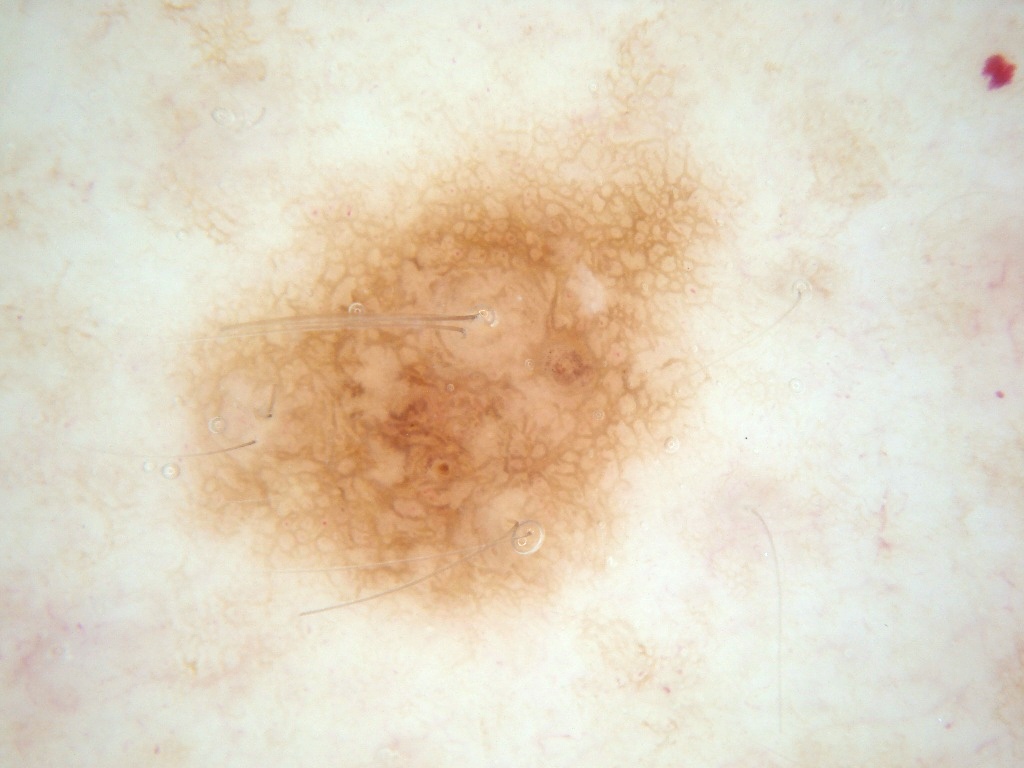<lesion>
<image>
  <modality>dermoscopy</modality>
</image>
<patient>
  <sex>female</sex>
  <age_approx>50</age_approx>
</patient>
<lesion_location>
  <bbox_xyxy>182, 133, 715, 610</bbox_xyxy>
</lesion_location>
<lesion_extent>moderate</lesion_extent>
<dermoscopic_features>
  <present>pigment network</present>
  <absent>globules, negative network, streaks, milia-like cysts</absent>
</dermoscopic_features>
<diagnosis>
  <name>melanocytic nevus</name>
  <malignancy>benign</malignancy>
  <lineage>melanocytic</lineage>
  <provenance>clinical</provenance>
</diagnosis>
</lesion>